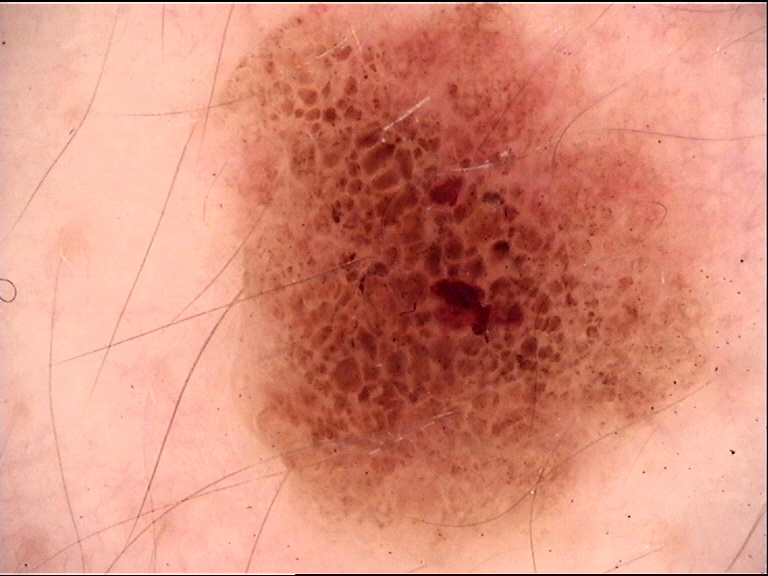Case:
* diagnostic label — compound nevus (expert consensus)